The photo was captured at an angle, the patient indicates the lesion is raised or bumpy.
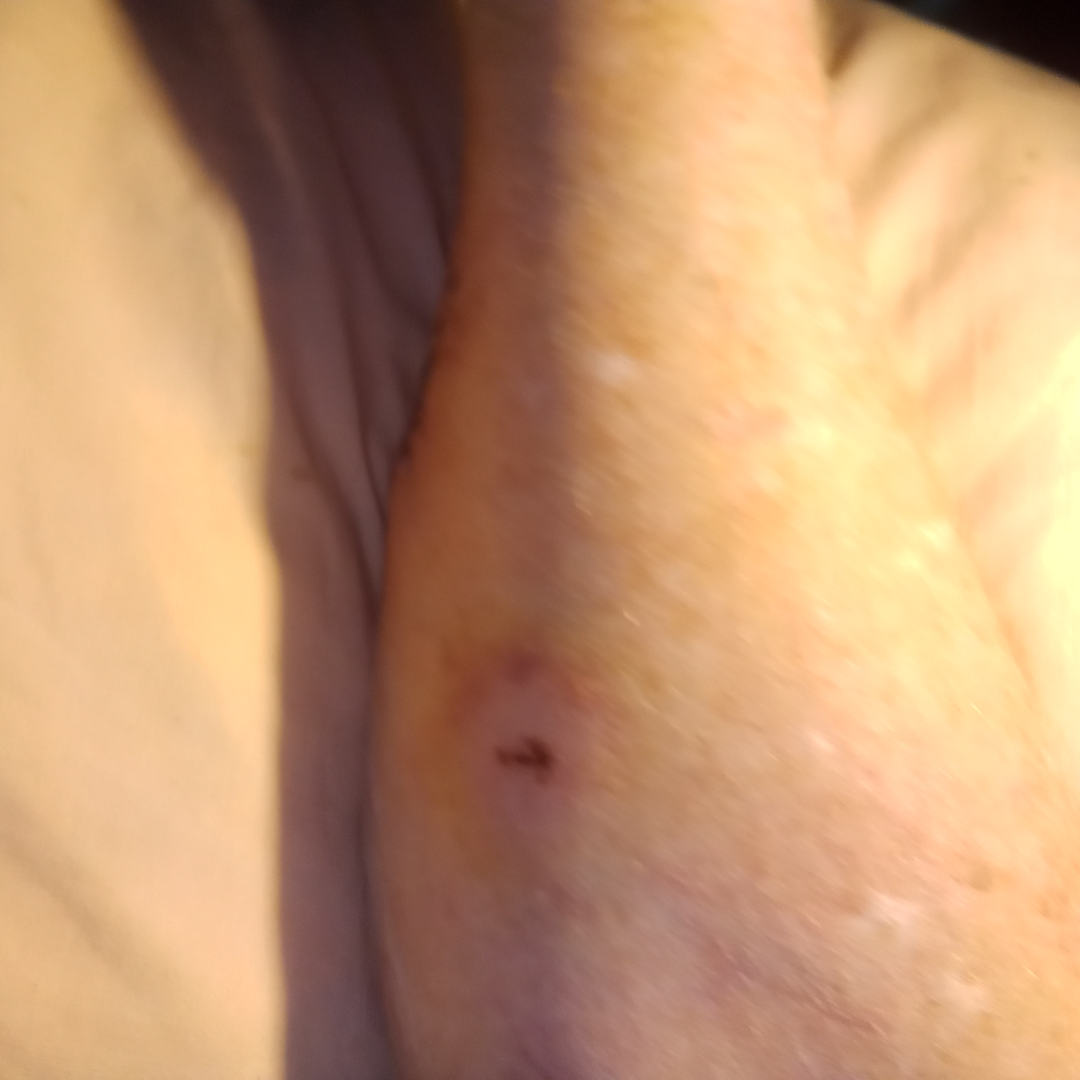Q: Could the case be diagnosed?
A: indeterminate from the photograph